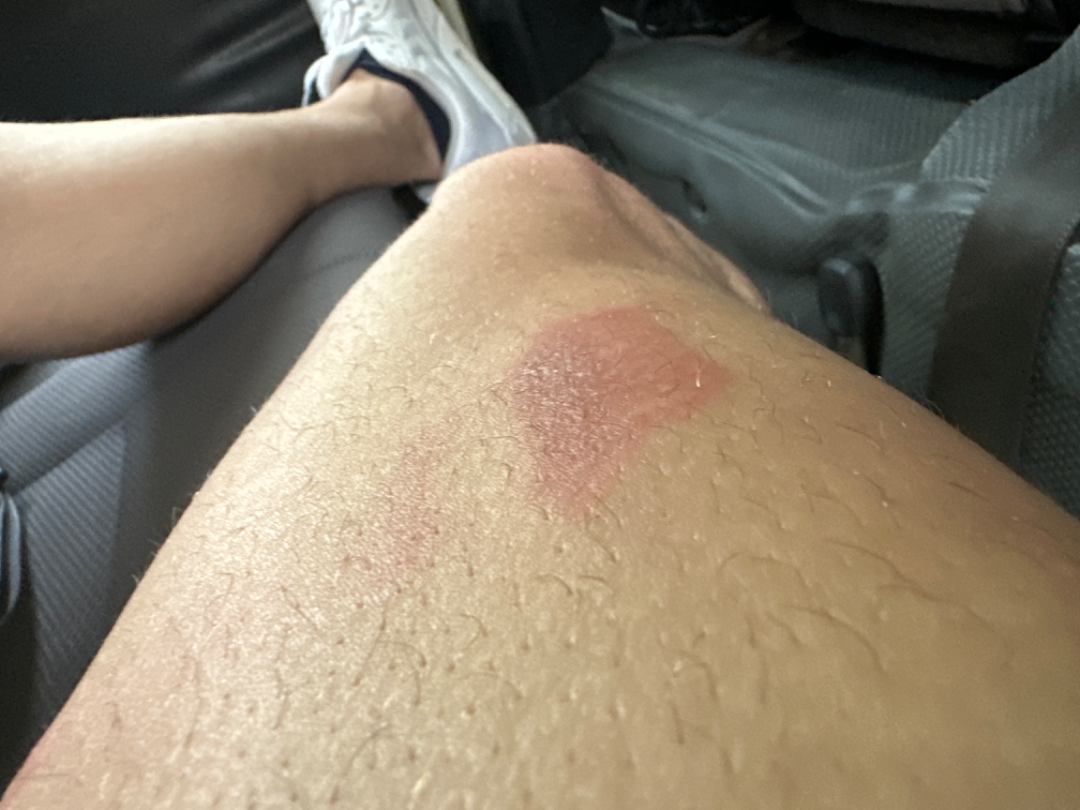impression=the differential includes Abrasion and/or friction burn of thigh without infection and Irritant Contact Dermatitis, with no clear leading consideration; less probable is Burn of skin; less likely is ecchymoses; lower on the differential is Allergic Contact Dermatitis.